A female subject approximately 40 years of age; dermoscopy of a skin lesion.
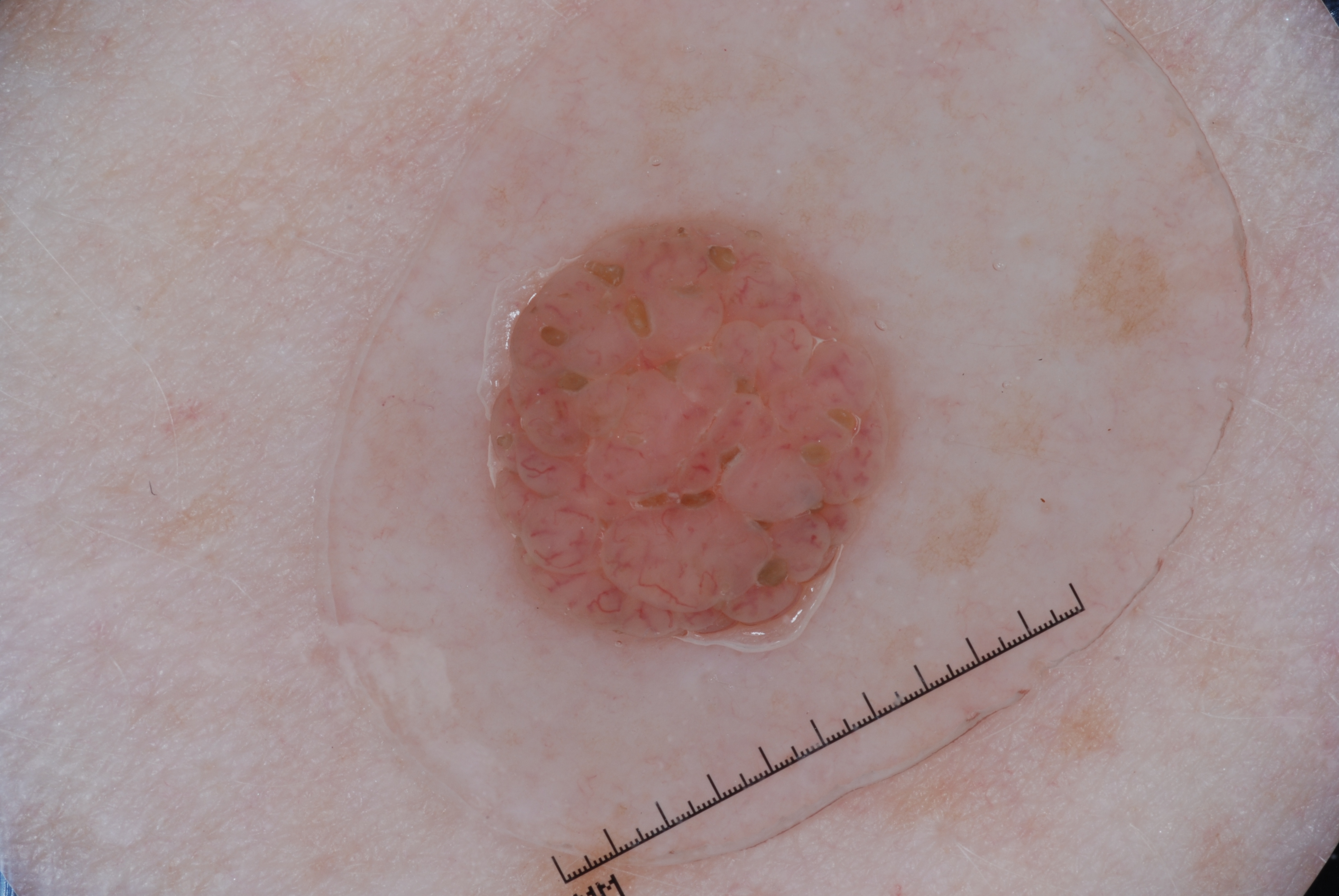| feature | finding |
|---|---|
| lesion bbox | x1=469 y1=195 x2=917 y2=669 |
| size | ~13% of the field |
| dermoscopic features not present | pigment network, streaks, milia-like cysts, and negative network |
| diagnosis | a melanocytic nevus, a benign lesion |